A male subject, about 55 years old. A skin lesion imaged with a dermatoscope: 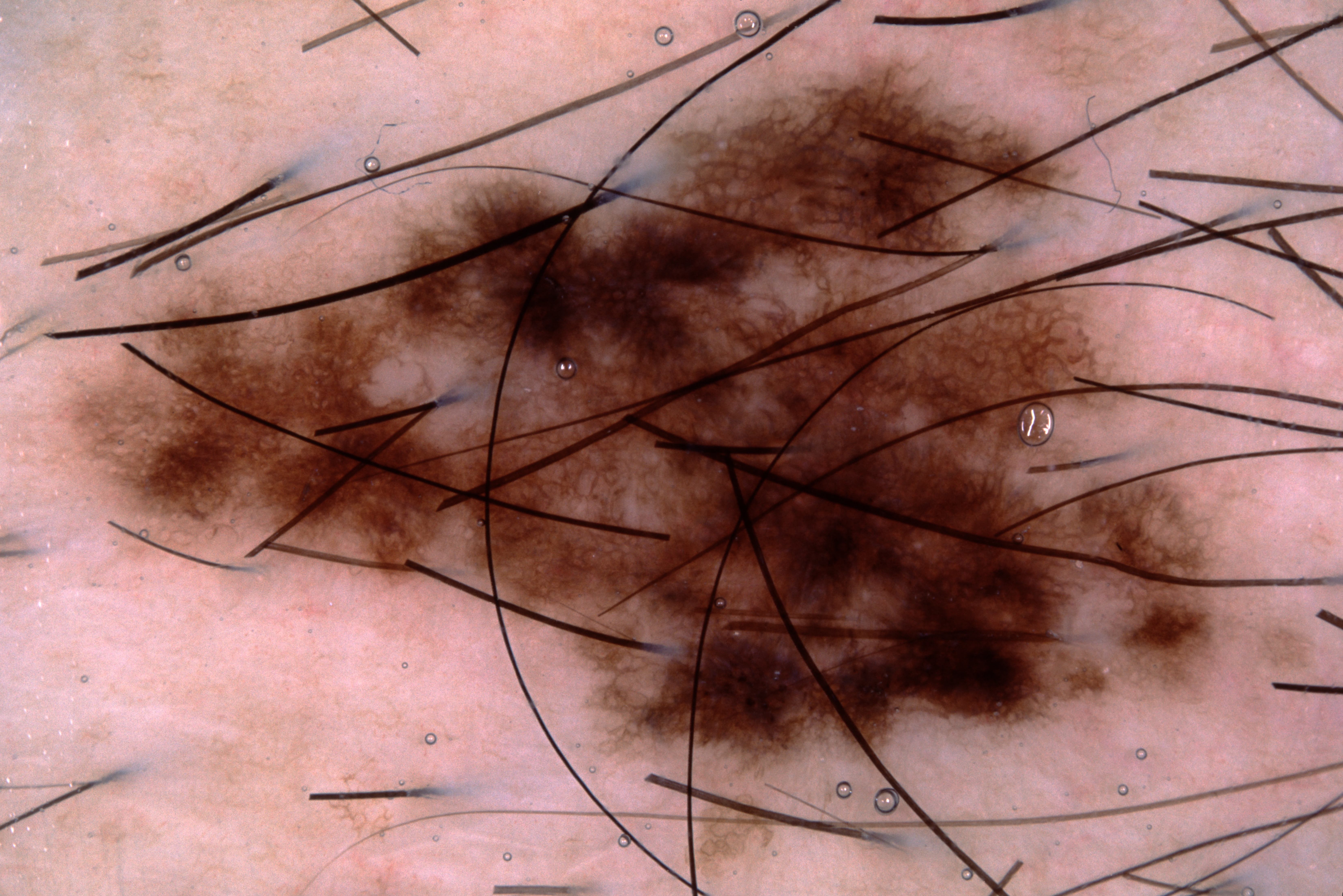{"lesion_location": {"bbox_xyxy": [74, 70, 1238, 763]}, "dermoscopic_features": {"present": ["pigment network"], "absent": ["streaks", "milia-like cysts", "negative network"]}, "lesion_extent": "large", "diagnosis": {"name": "melanocytic nevus", "malignancy": "benign", "lineage": "melanocytic", "provenance": "clinical"}}